Contact-polarized dermoscopy of a skin lesion. A female subject roughly 50 years of age. The chart records a prior melanoma.
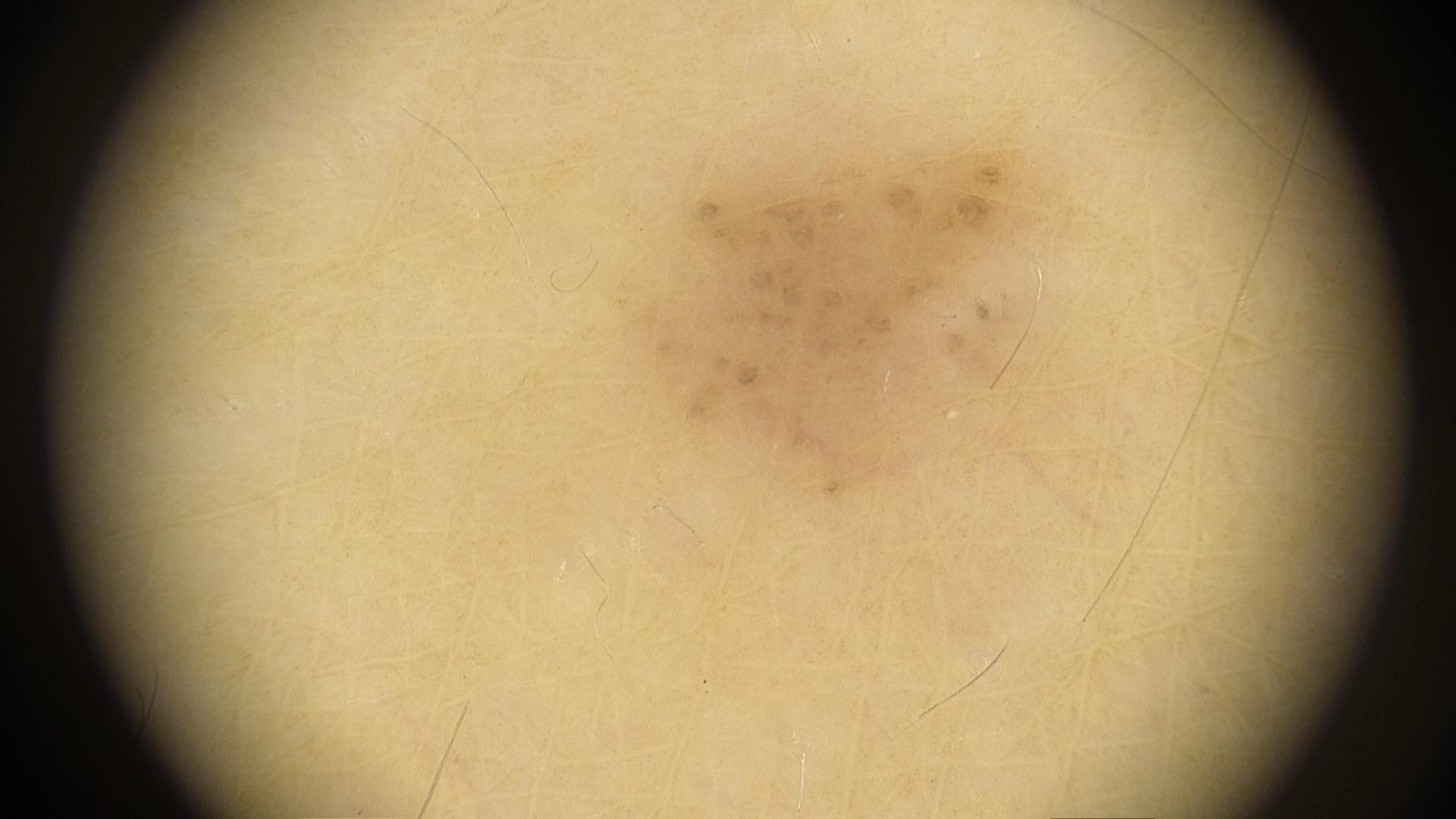The lesion involves a lower extremity.
Consistent with a lesion of melanocytic origin — a nevus.